Dermoscopy of a skin lesion; a male patient, roughly 65 years of age:
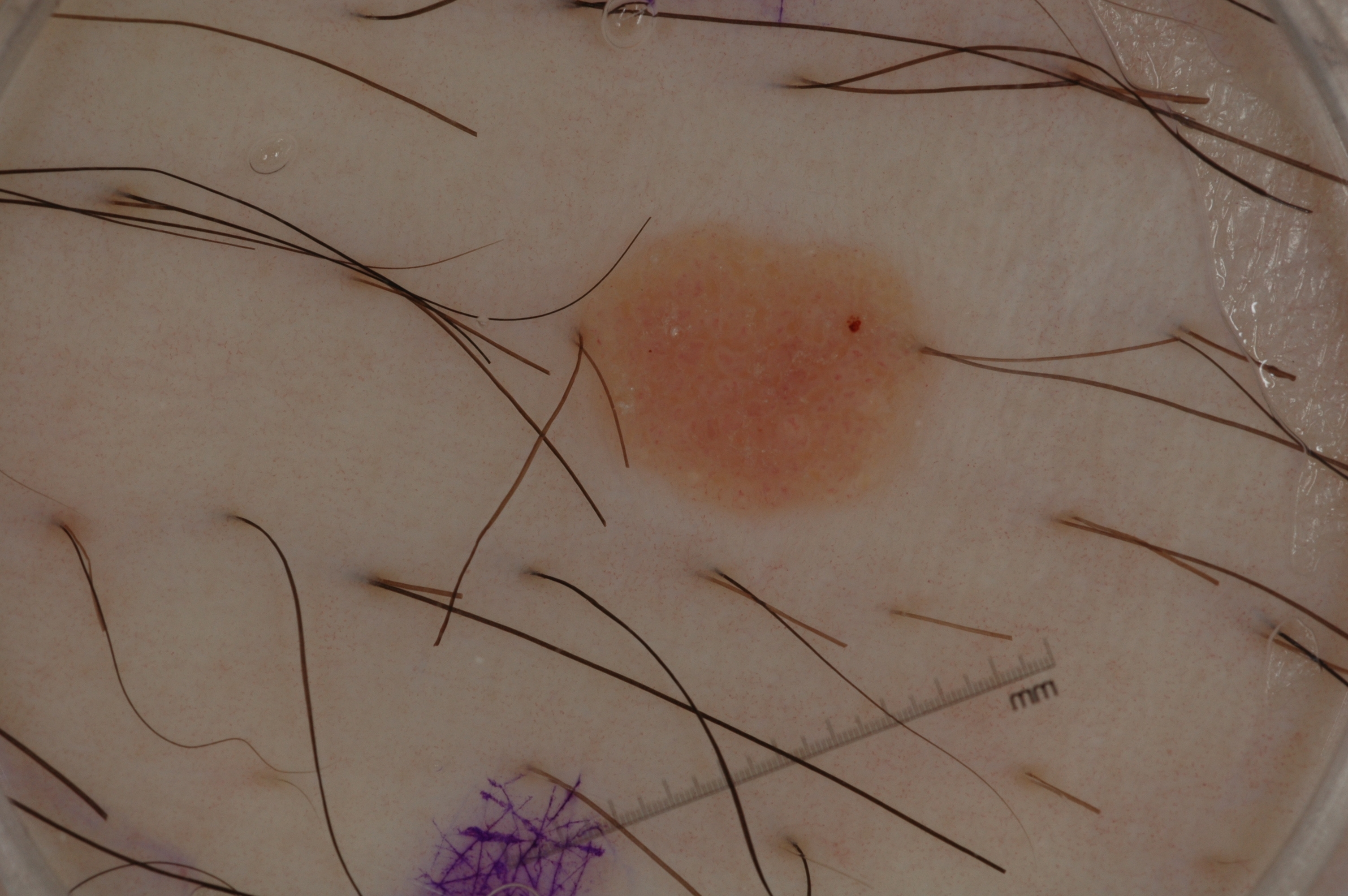Case summary: Dermoscopic examination shows milia-like cysts; no negative network, pigment network, or streaks. A small lesion occupying a minor part of the field. As (left, top, right, bottom), the lesion is bounded by (569, 231, 937, 511). Assessment: Diagnosed as a seborrheic keratosis, a benign skin lesion.